A dermoscopy image of a single skin lesion.
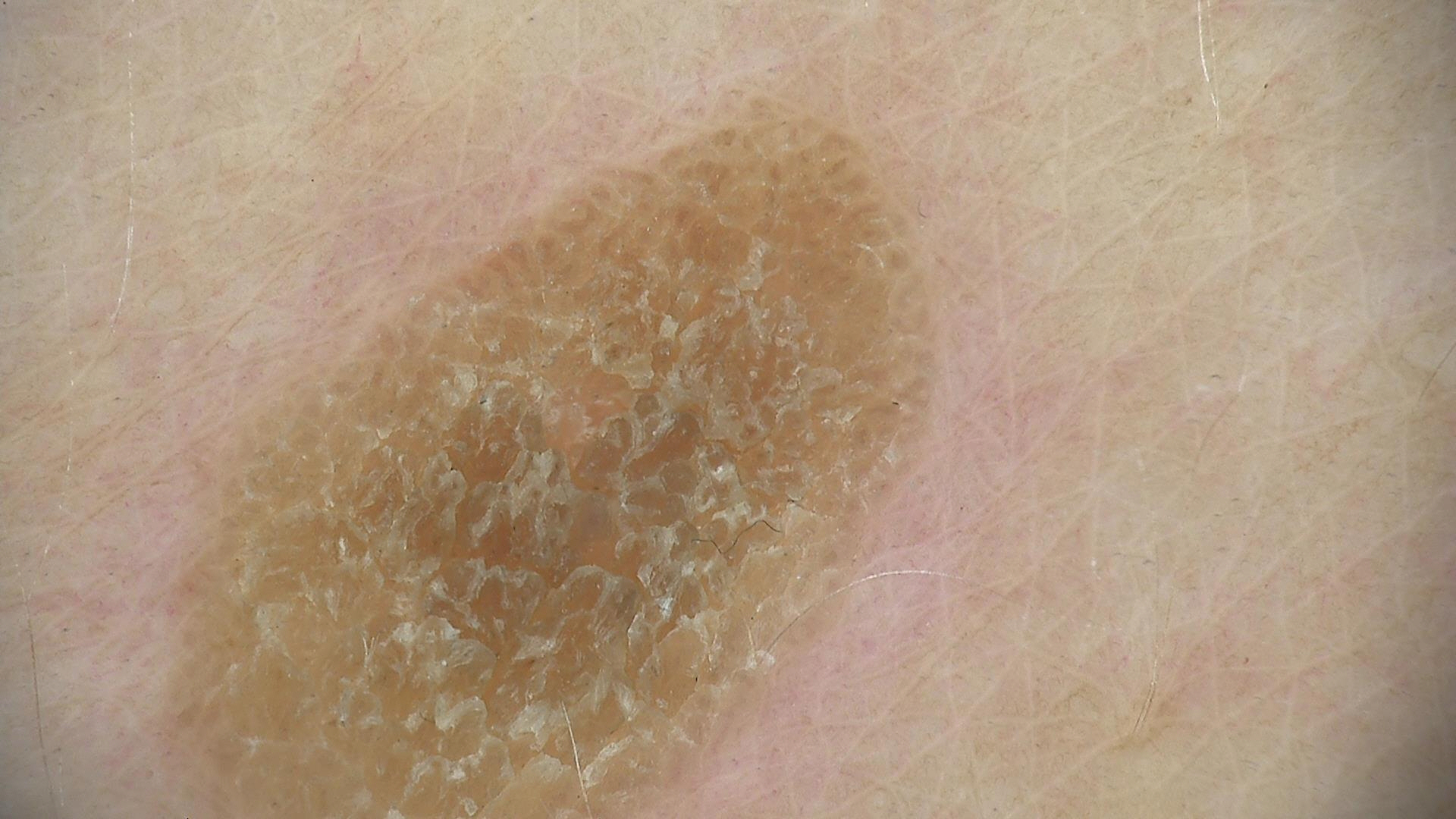Summary: This is a keratinocytic lesion. Conclusion: Labeled as a seborrheic keratosis.